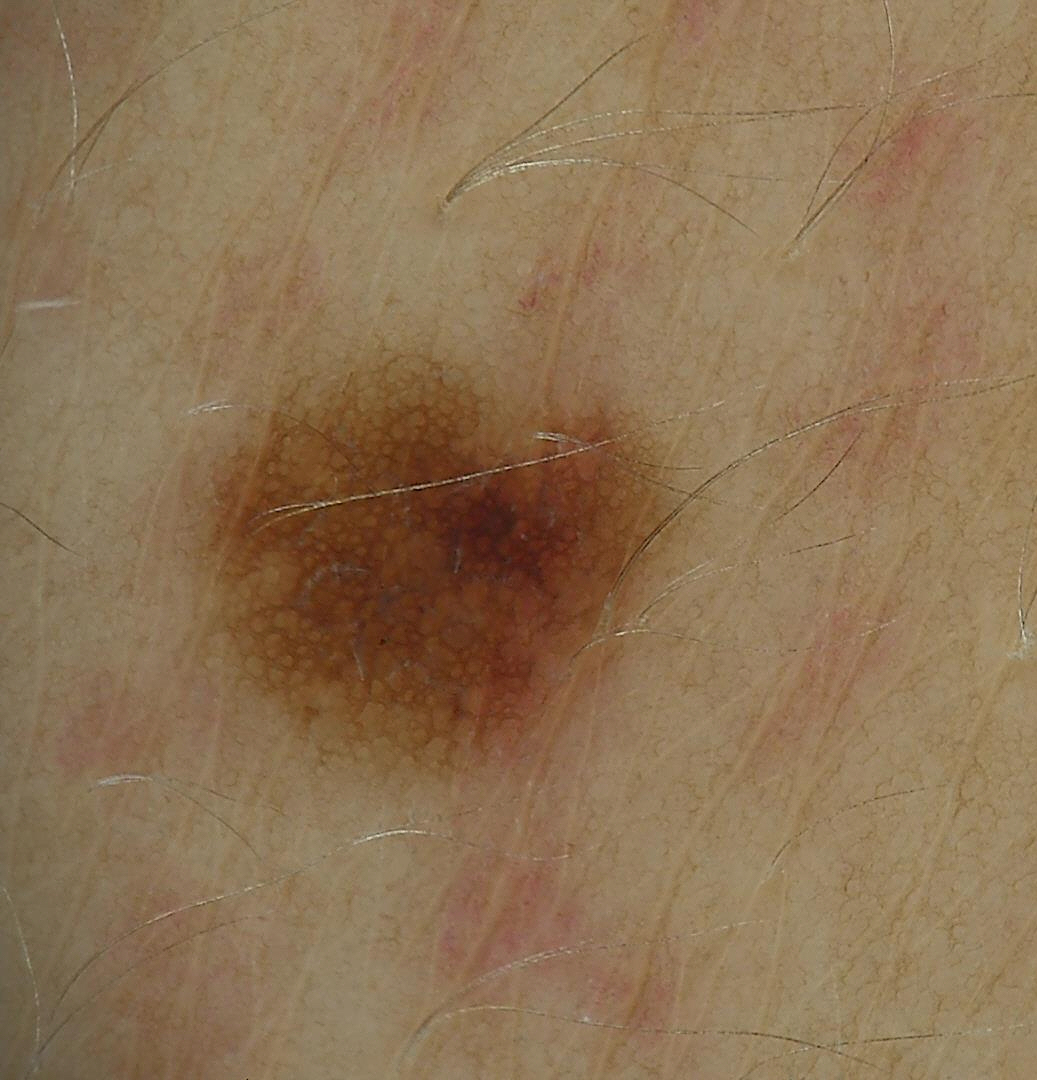image = dermoscopy, class = dysplastic junctional nevus (expert consensus).